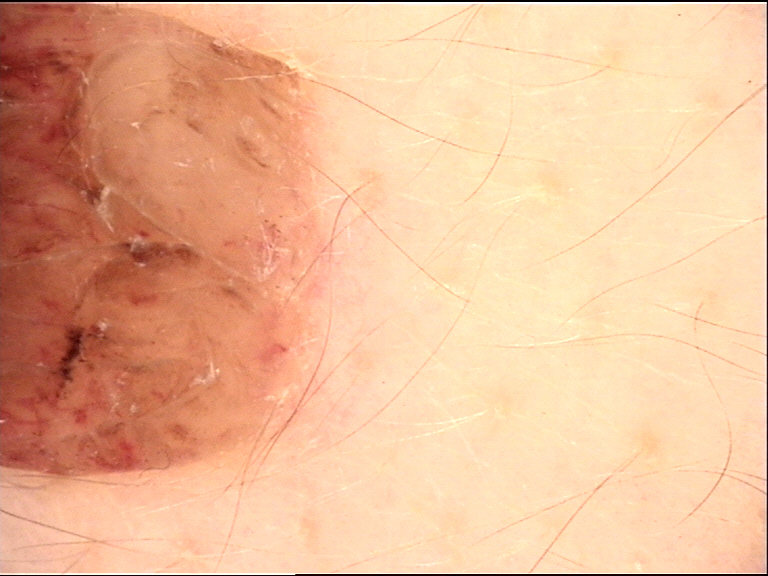• image type: dermoscopy
• classification: banal
• class: dermal nevus (expert consensus)